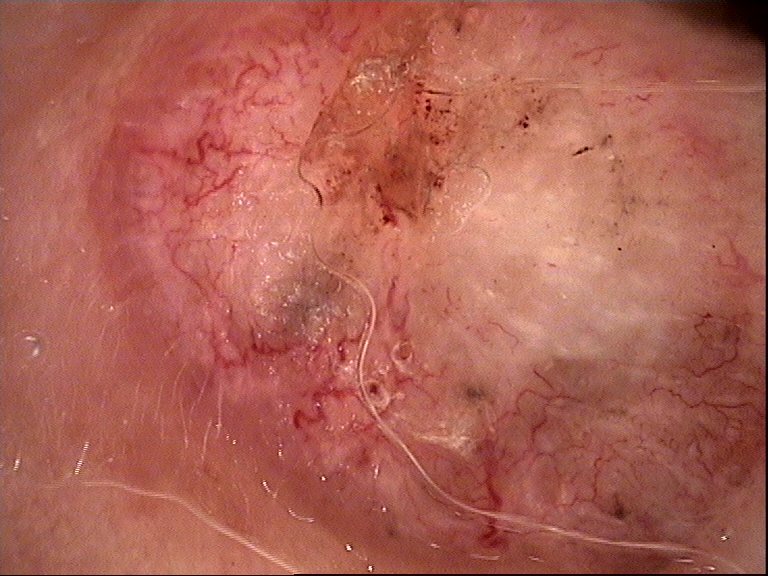subtype — keratinocytic | pathology — basal cell carcinoma (biopsy-proven).